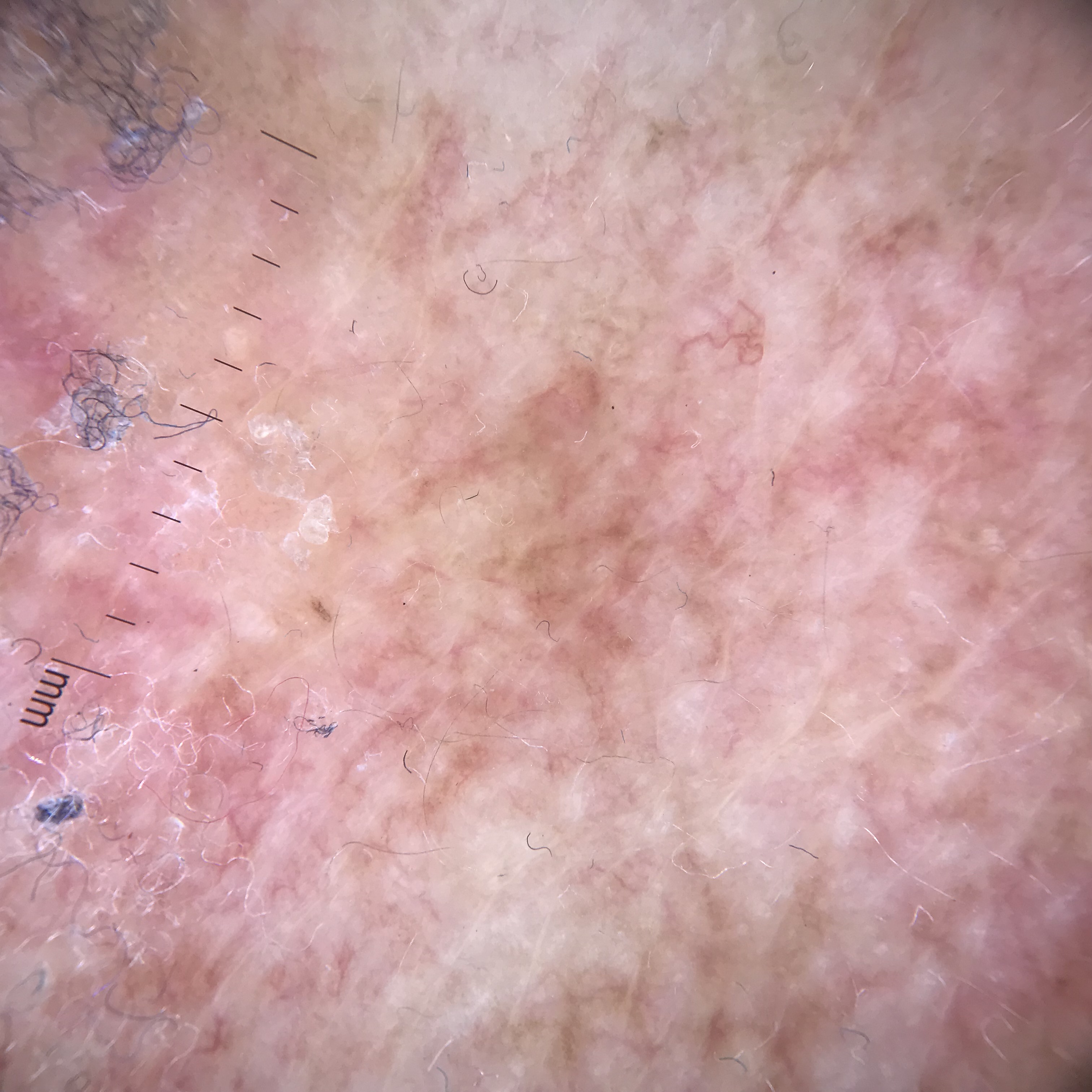| feature | finding |
|---|---|
| assessment | actinic keratosis (expert consensus) |